The subject is a female aged 50–59, an image taken at an angle, located on the arm: 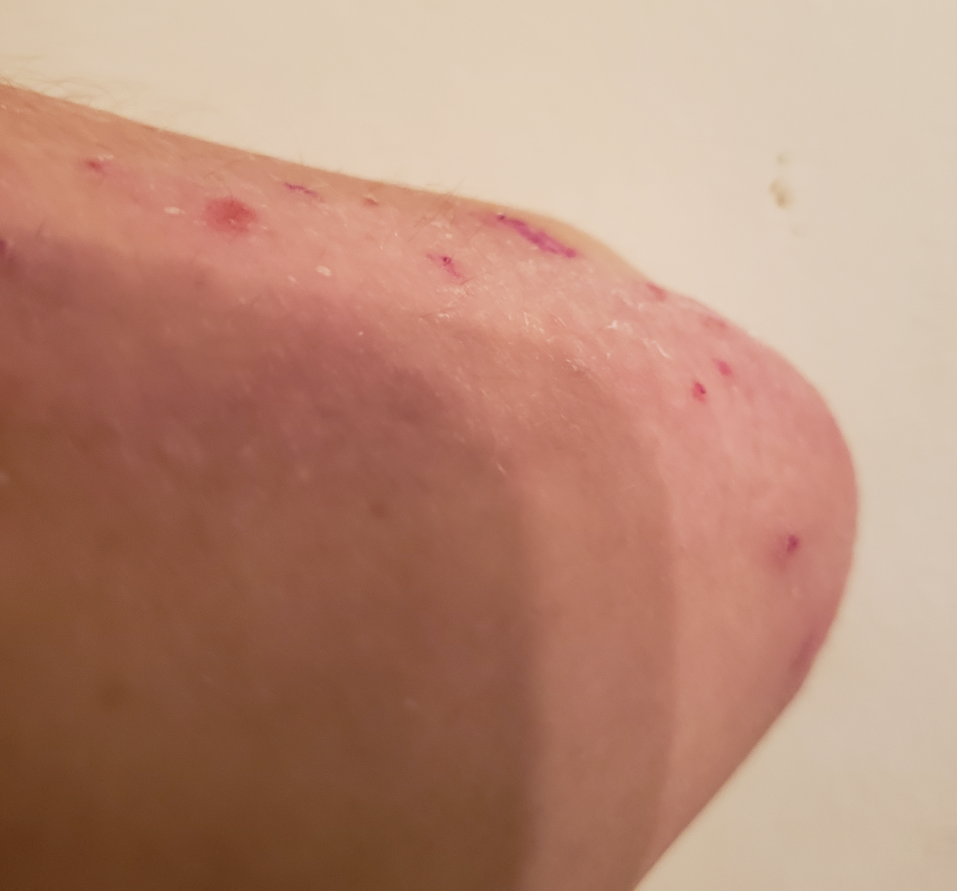diagnostic considerations: Psoriasis (primary).